The photo was captured at an angle, the leg and arm are involved — 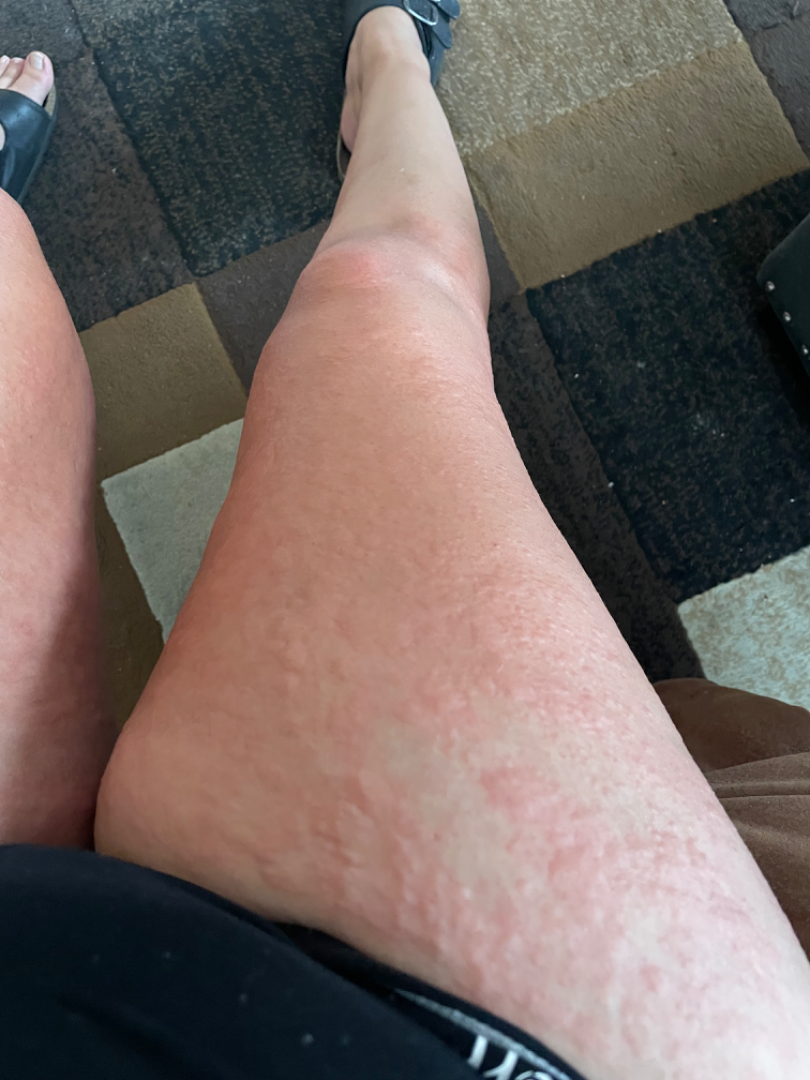clinical impression=most likely Urticaria.